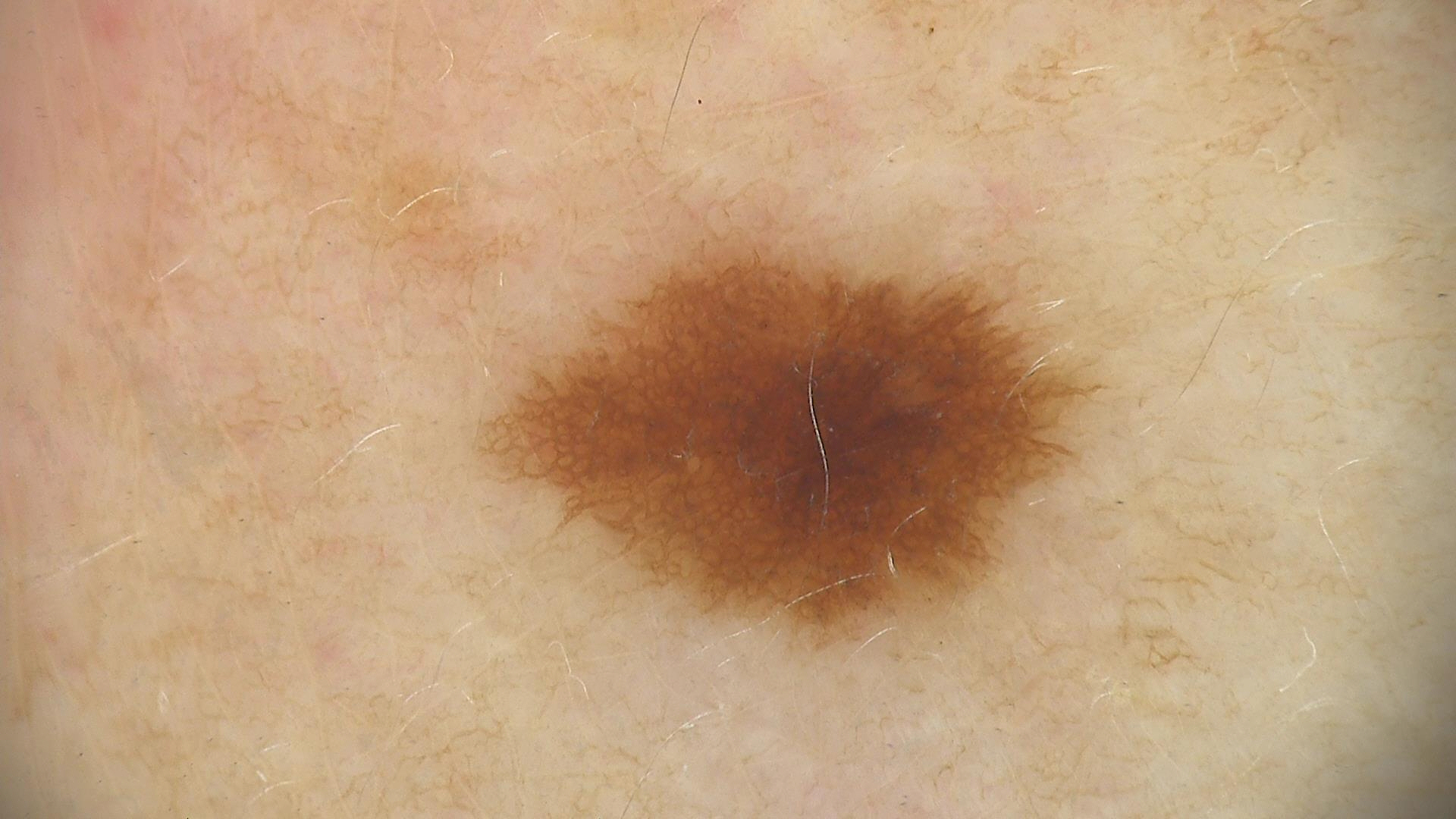A dermoscopic close-up of a skin lesion. The diagnosis was a benign lesion — a dysplastic junctional nevus.